Dermoscopy of a skin lesion.
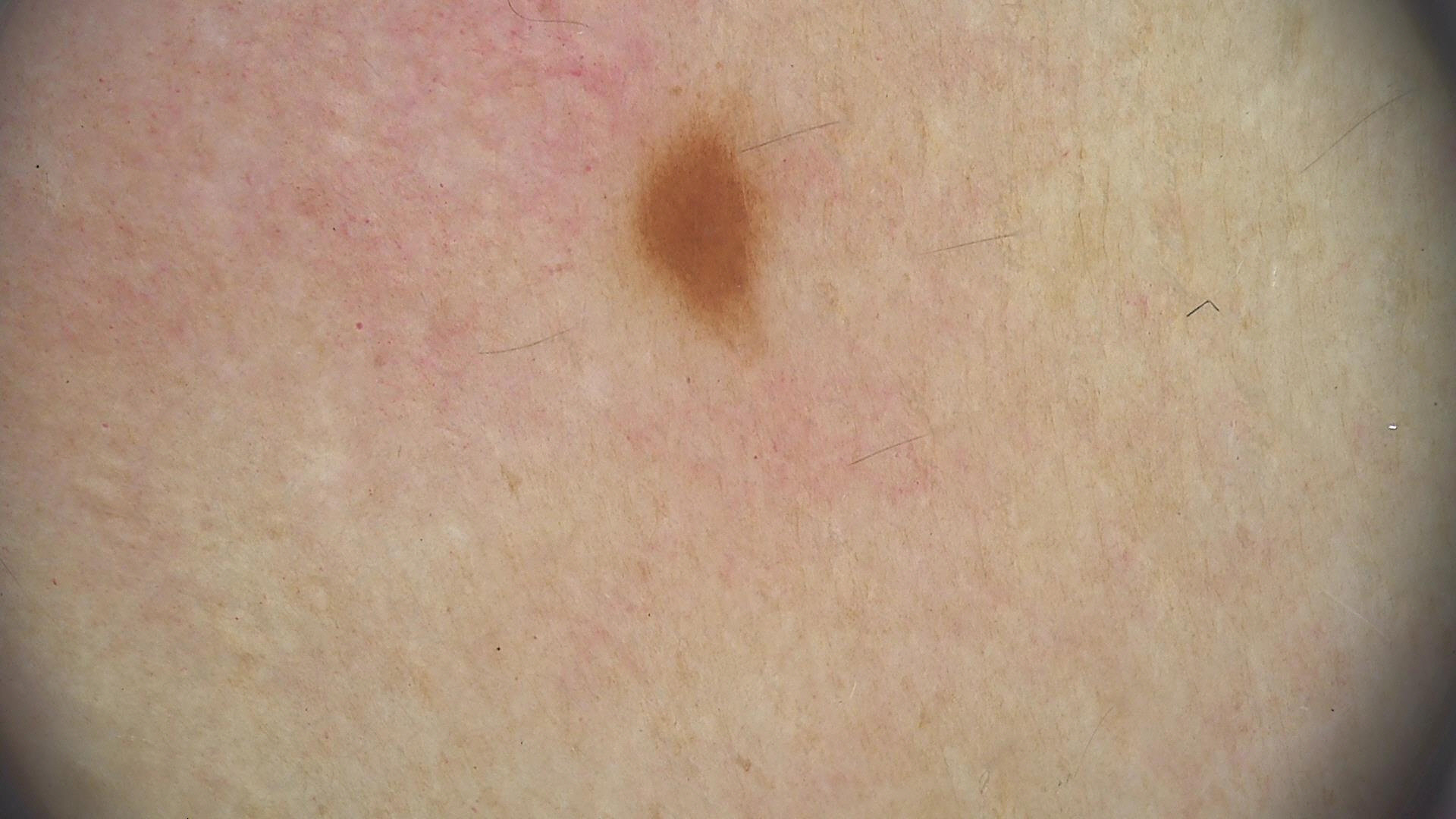diagnosis: junctional nevus (expert consensus).